A dermoscopic image of a skin lesion.
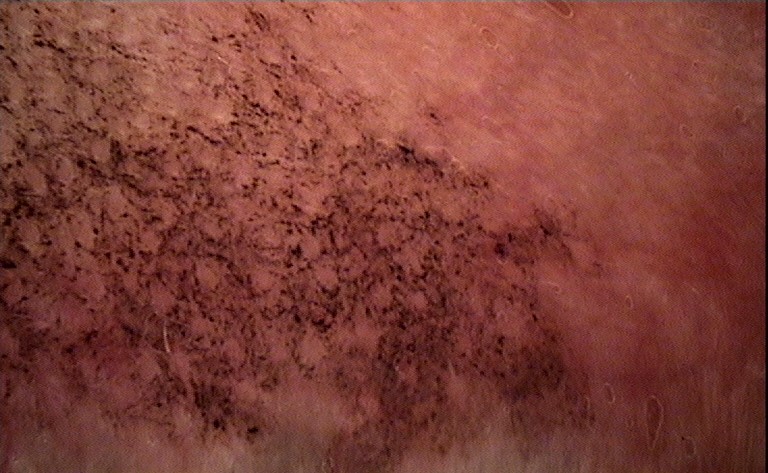{"diagnosis": {"name": "ink-spot lentigo", "code": "isl", "malignancy": "benign", "super_class": "melanocytic", "confirmation": "expert consensus"}}